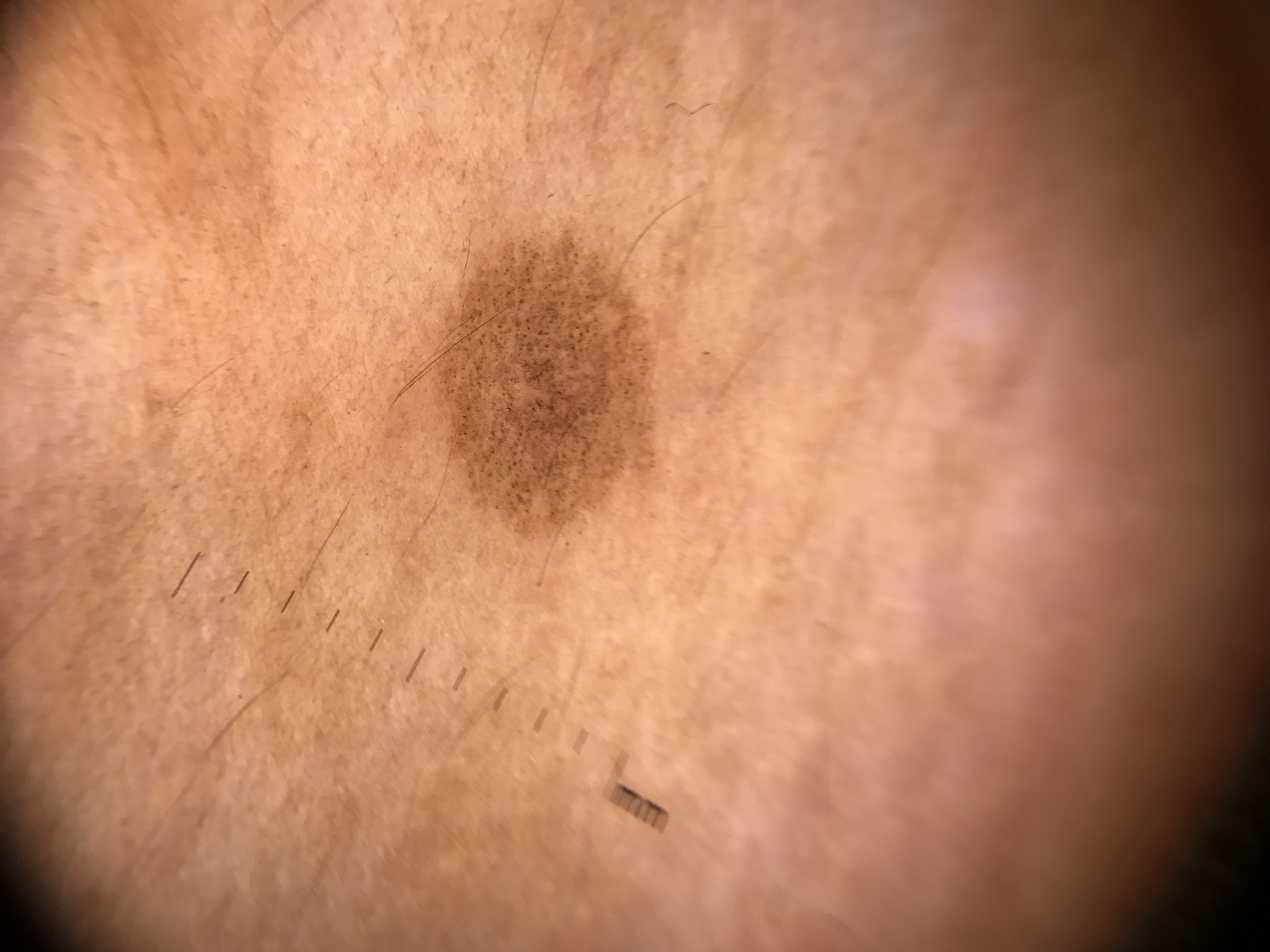Q: What is the imaging modality?
A: dermatoscopy
Q: What was the diagnostic impression?
A: junctional nevus (expert consensus)